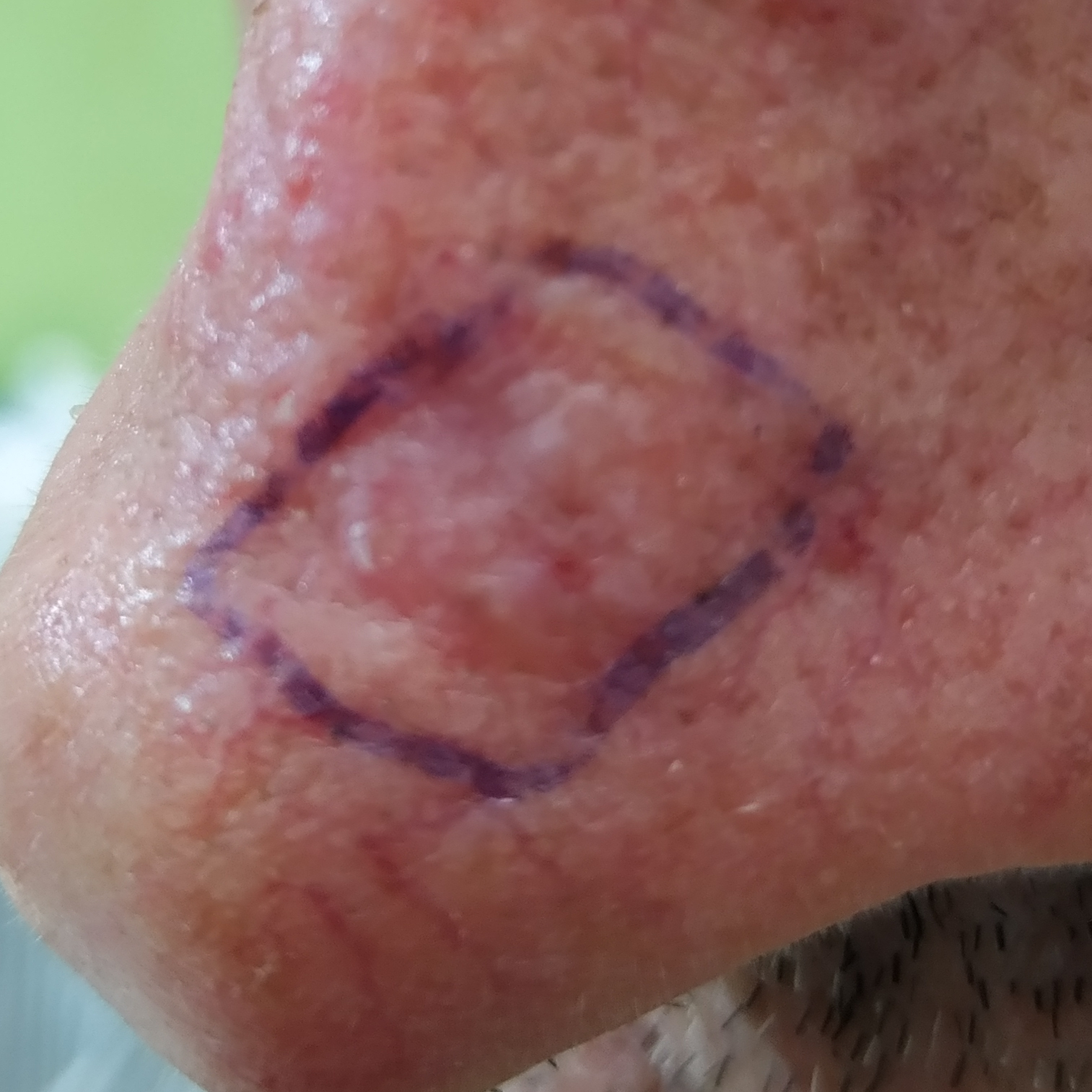A clinical photo of a skin lesion taken with a smartphone. A male subject in their 50s. Histopathology confirmed a basal cell carcinoma.